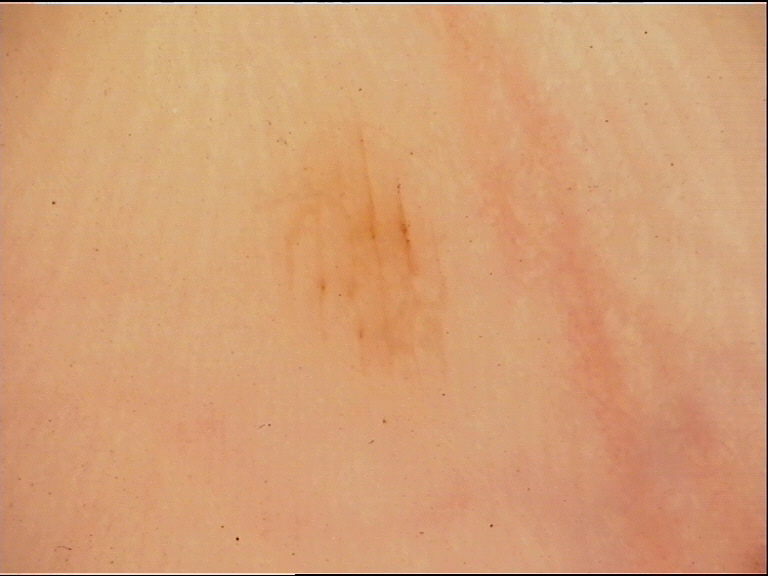A dermoscopy image of a single skin lesion.
Diagnosed as a banal lesion — an acral junctional nevus.